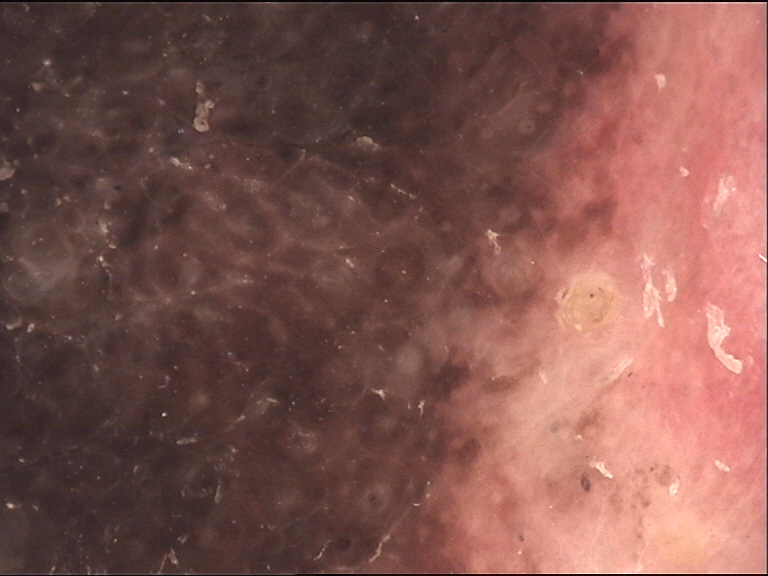Consistent with a banal lesion — a congenital compound nevus.